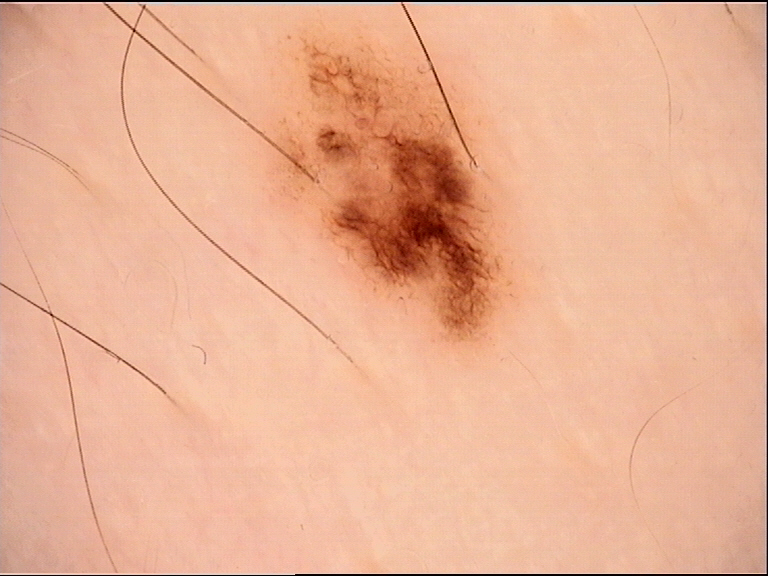<case>
  <image>dermoscopy</image>
  <diagnosis>
    <name>dysplastic junctional nevus</name>
    <code>jd</code>
    <malignancy>benign</malignancy>
    <super_class>melanocytic</super_class>
    <confirmation>expert consensus</confirmation>
  </diagnosis>
</case>